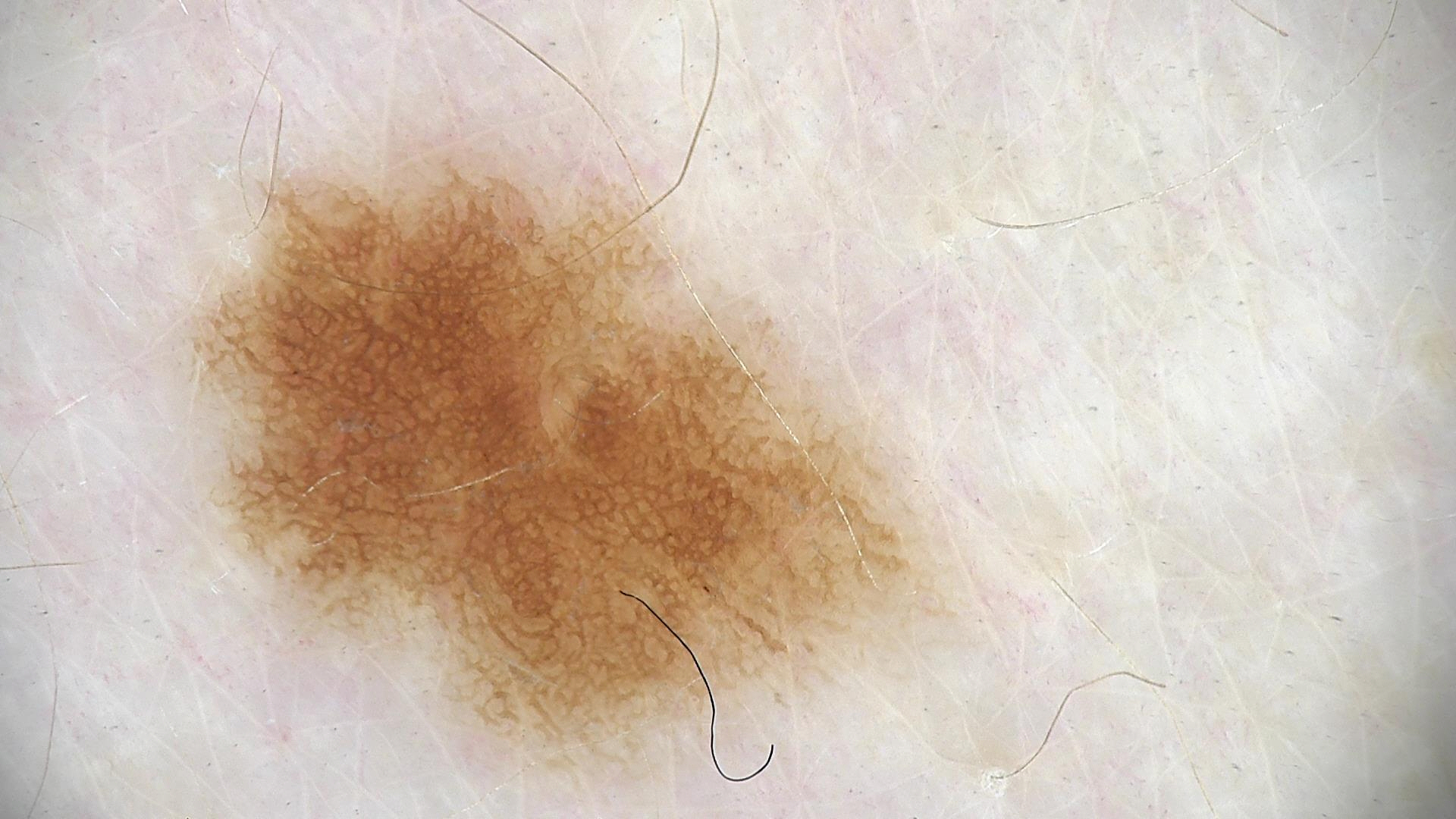– assessment: dysplastic junctional nevus (expert consensus)